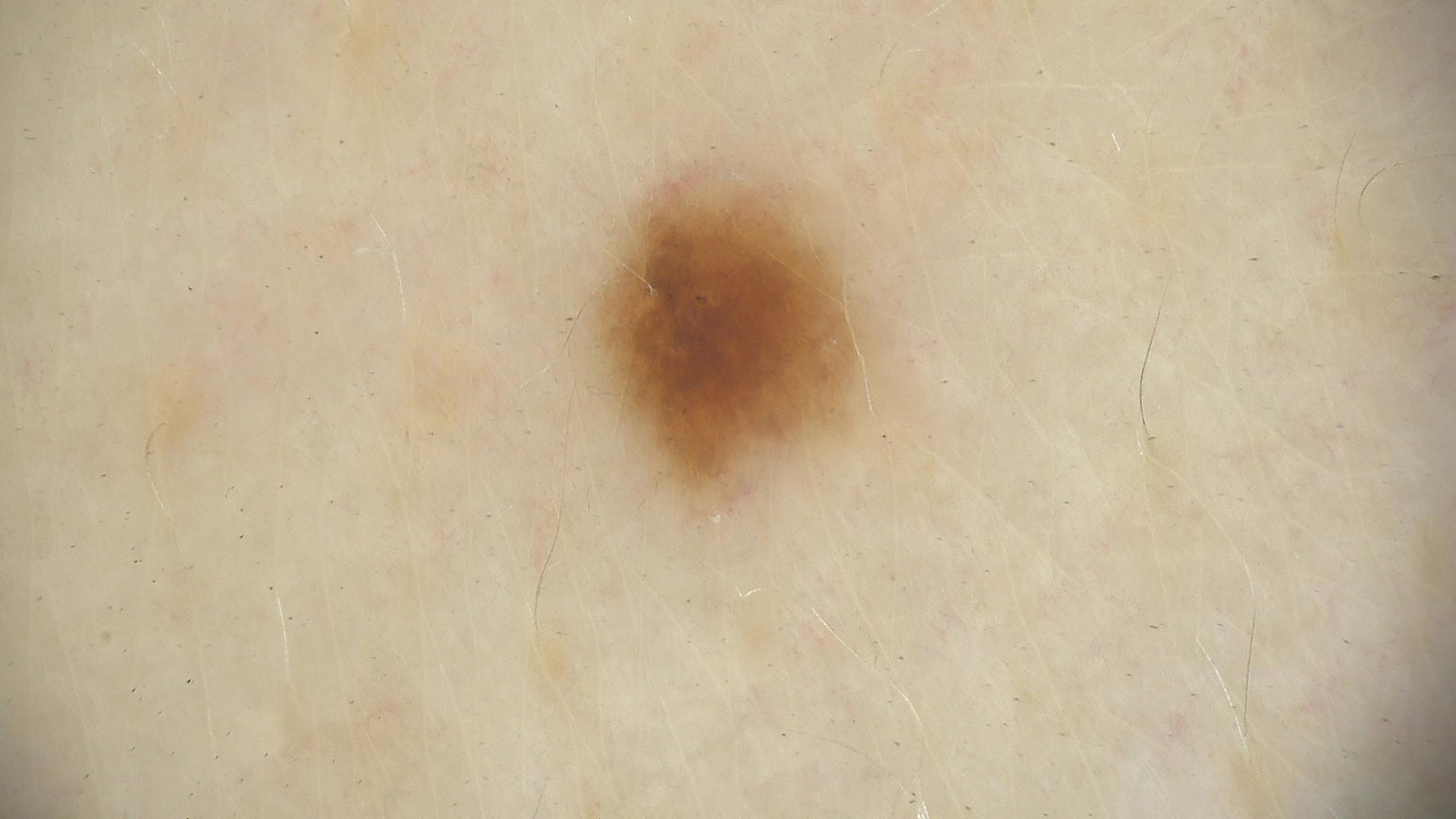{"diagnosis": {"name": "dysplastic junctional nevus", "code": "jd", "malignancy": "benign", "super_class": "melanocytic", "confirmation": "expert consensus"}}